Female subject, age 40–49. The photo was captured at an angle. The lesion involves the front of the torso.
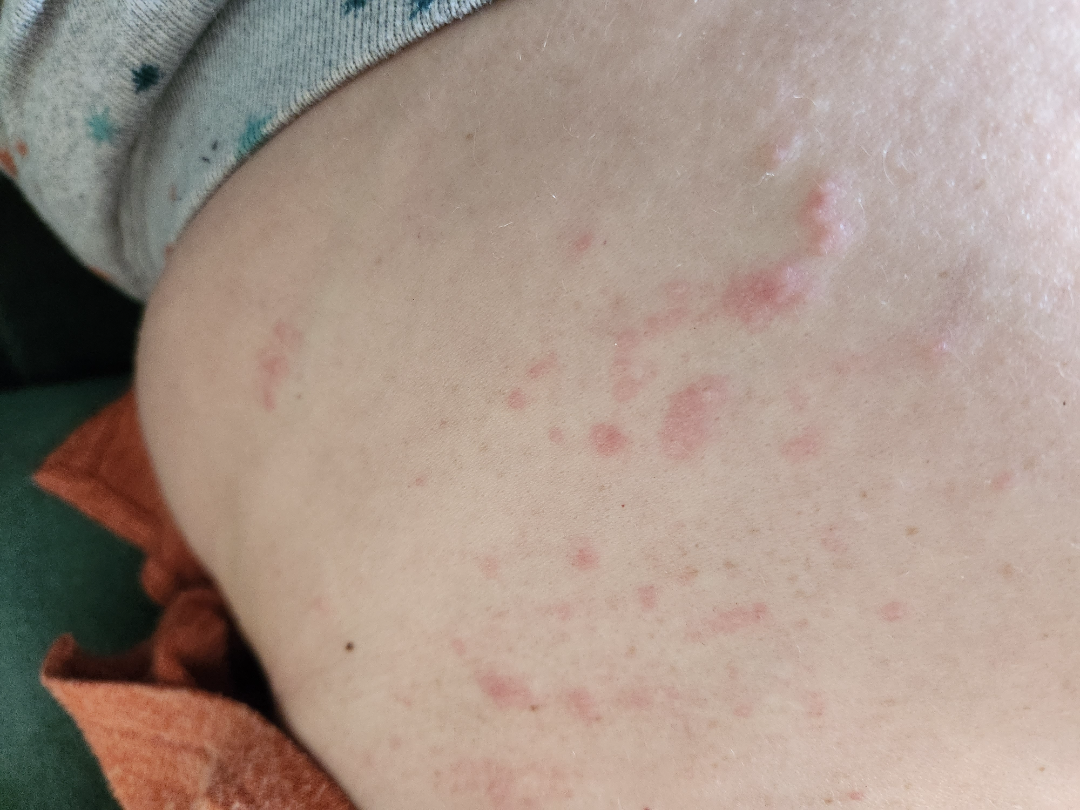Impression: Most consistent with Irritant Contact Dermatitis; with consideration of Herpes Zoster; also consider Allergic Contact Dermatitis; less probable is Eczema.